The subject is 18–29, female; the lesion involves the arm; the patient notes the lesion is rough or flaky; the patient described the issue as a rash; symptoms reported: enlargement; close-up view — 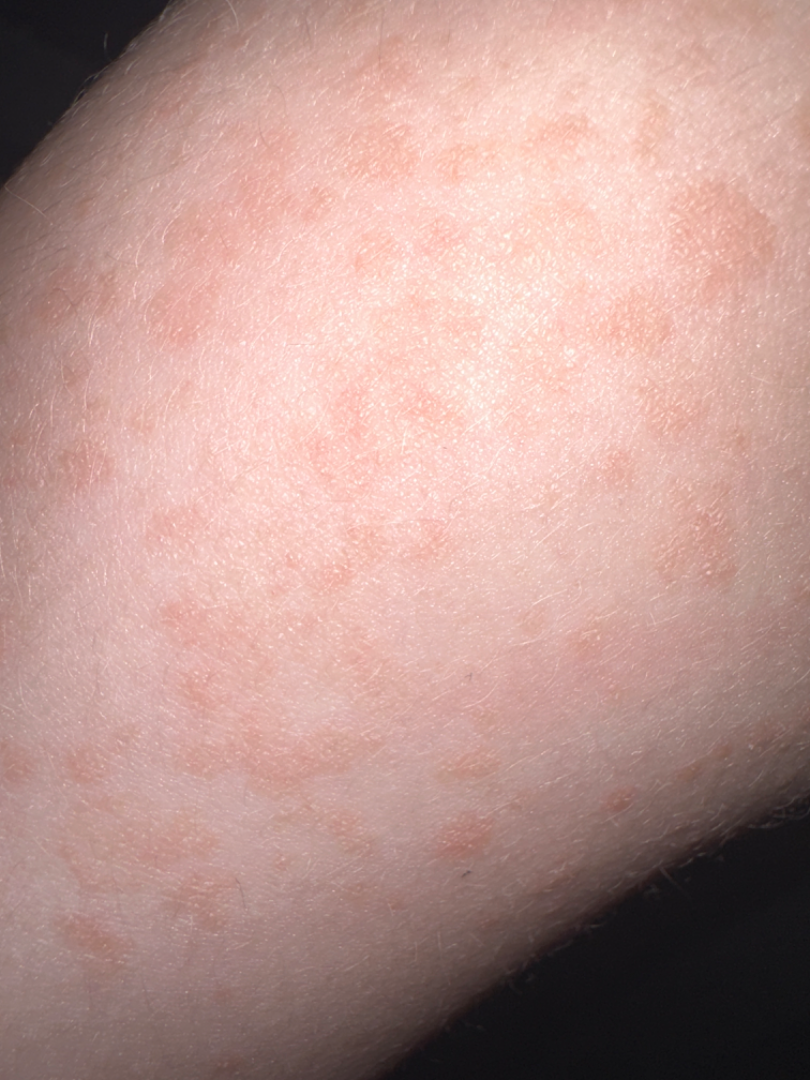The skin findings could not be characterized from the image.